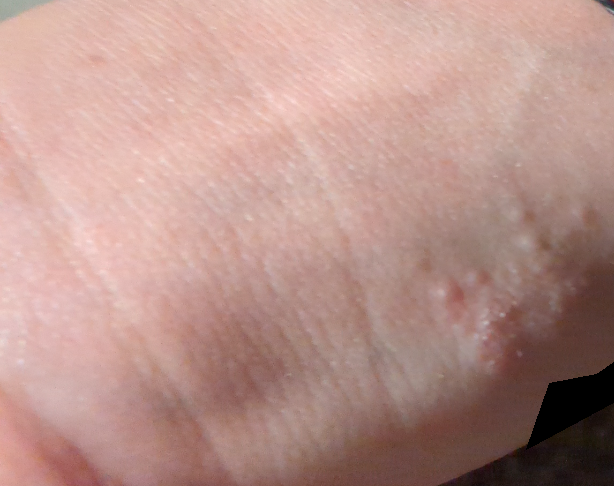associated systemic symptoms — fatigue
site — arm and leg
history — one to four weeks
reported symptoms — enlargement and itching
view — close-up
described texture — raised or bumpy, rough or flaky and fluid-filled
patient's own categorization — a rash
contributor — female, age 18–29
dermatologist impression — most likely Allergic Contact Dermatitis; with consideration of Contact dermatitis; less likely is Eczema; lower on the differential is Irritant Contact Dermatitis; less probable is Herpes Simplex